A dermoscopy image of a single skin lesion. A male subject, in their 50s — 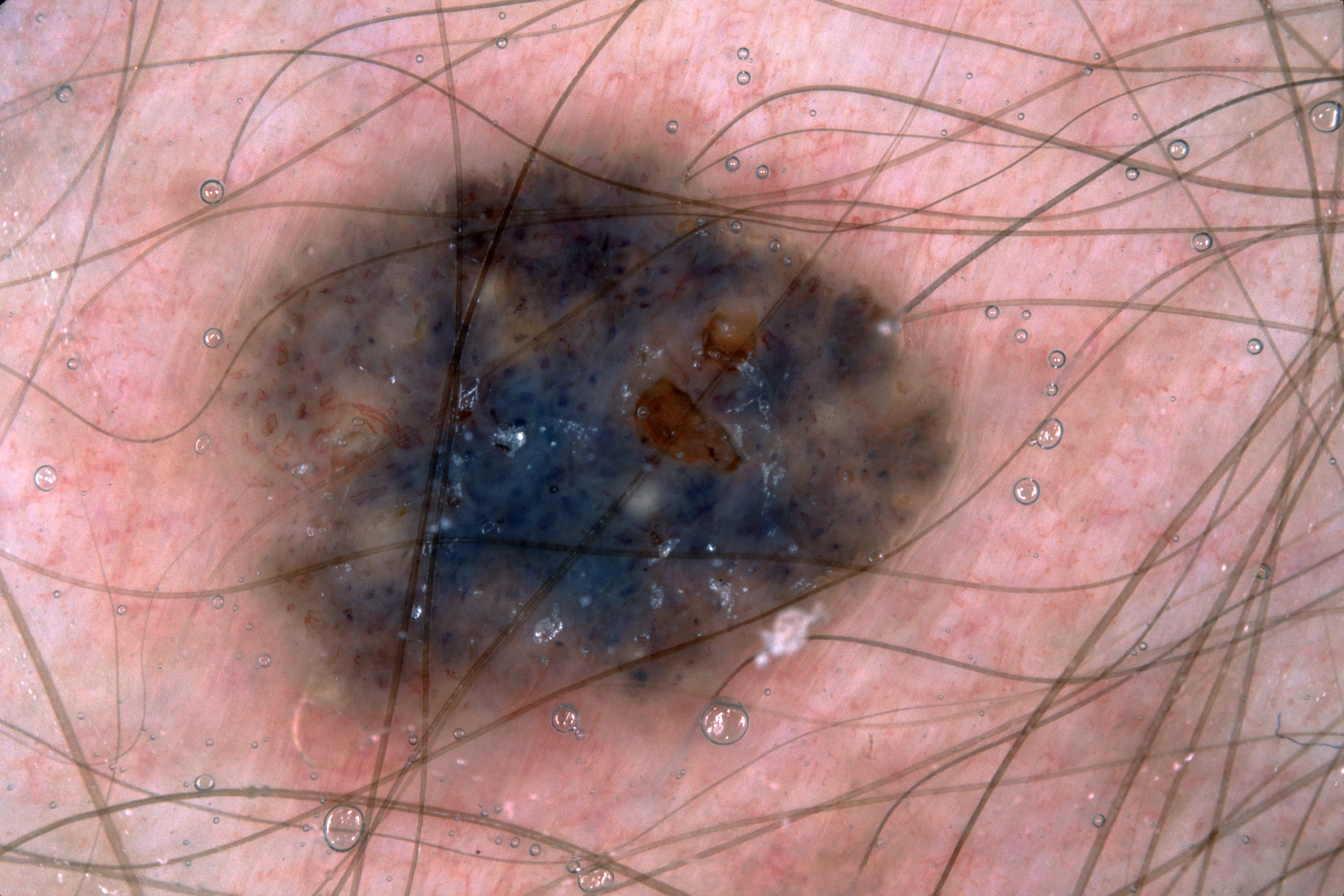  dermoscopic_features:
    present:
      - milia-like cysts
    absent:
      - pigment network
      - streaks
      - negative network
  lesion_location:
    bbox_xyxy:
      - 231
      - 133
      - 955
      - 742
  diagnosis:
    name: seborrheic keratosis
    malignancy: benign
    lineage: keratinocytic
    provenance: clinical